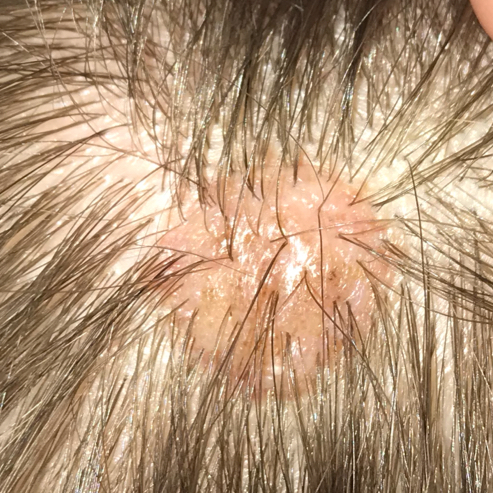A subject 21 years of age. A clinical photograph showing a skin lesion. The lesion was found on the scalp. The patient describes that the lesion is elevated and has grown, but has not changed and has not bled. The diagnostic impression was a benign lesion — a nevus.